A close-up photograph · the affected area is the arm.
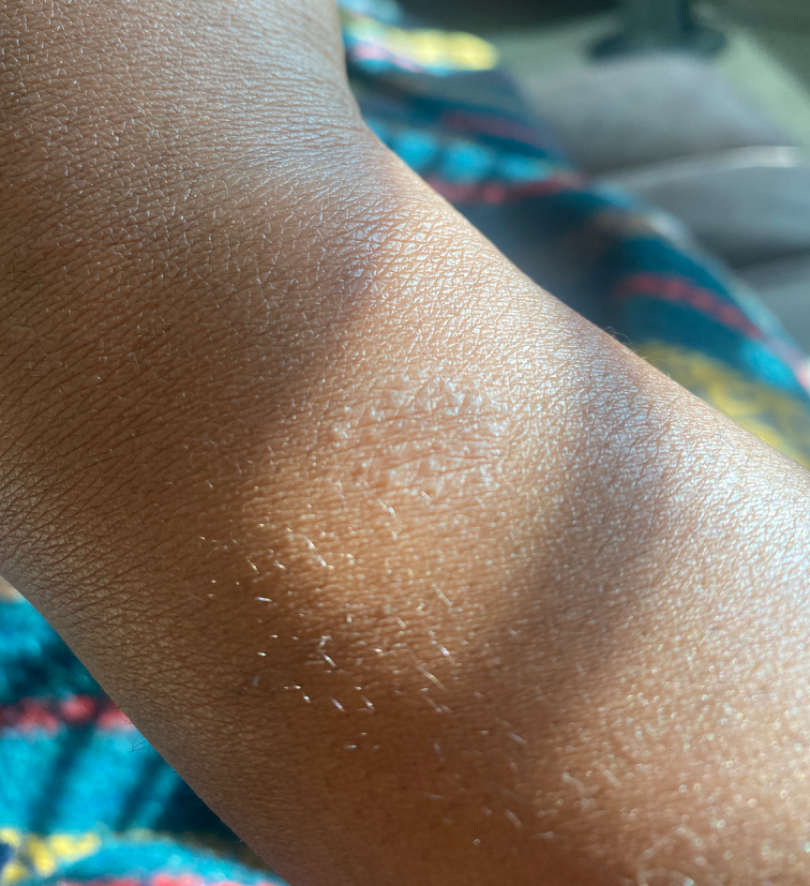The skin findings could not be characterized from the image. Reported lesion symptoms include enlargement and bothersome appearance.